Symptoms reported: pain, itching, burning and darkening. Self-categorized by the patient as a rash. The contributor reports associated joint pain and fatigue. A close-up photograph. The contributor reports the lesion is rough or flaky: 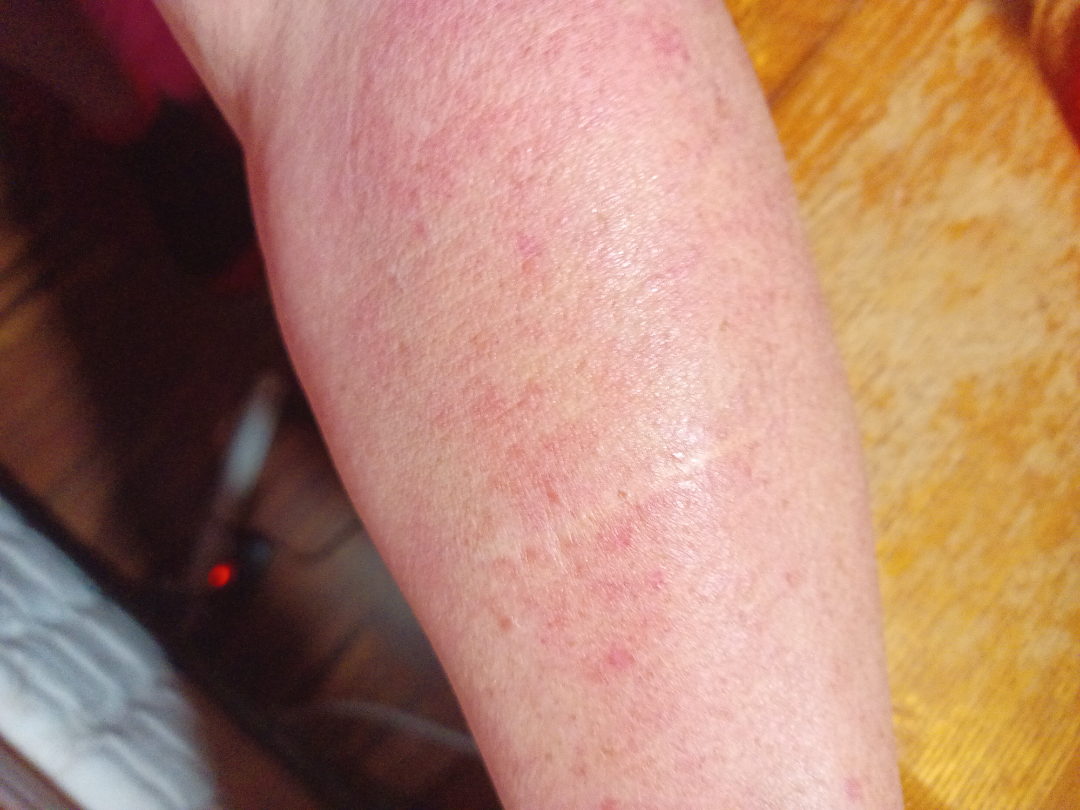On photographic review: most consistent with Acute dermatitis, NOS.